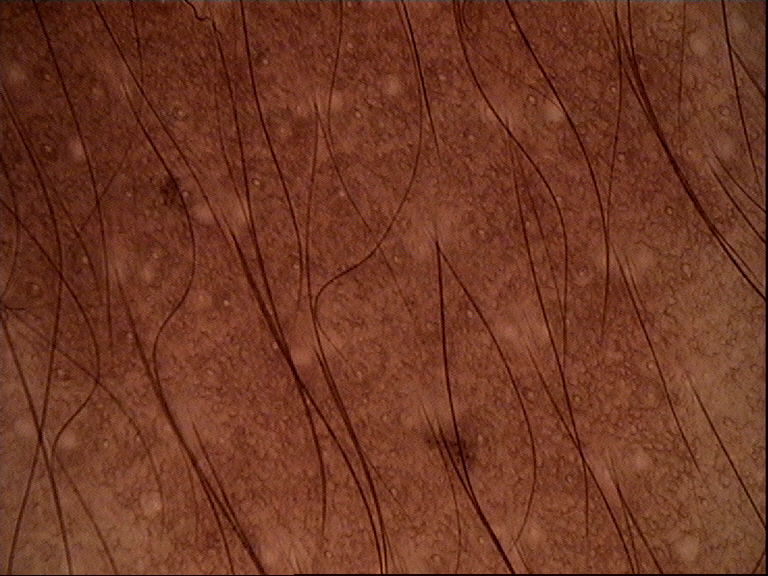diagnostic label: congenital junctional nevus (expert consensus).